A subject in their 50s · a clinical photograph showing a skin lesion.
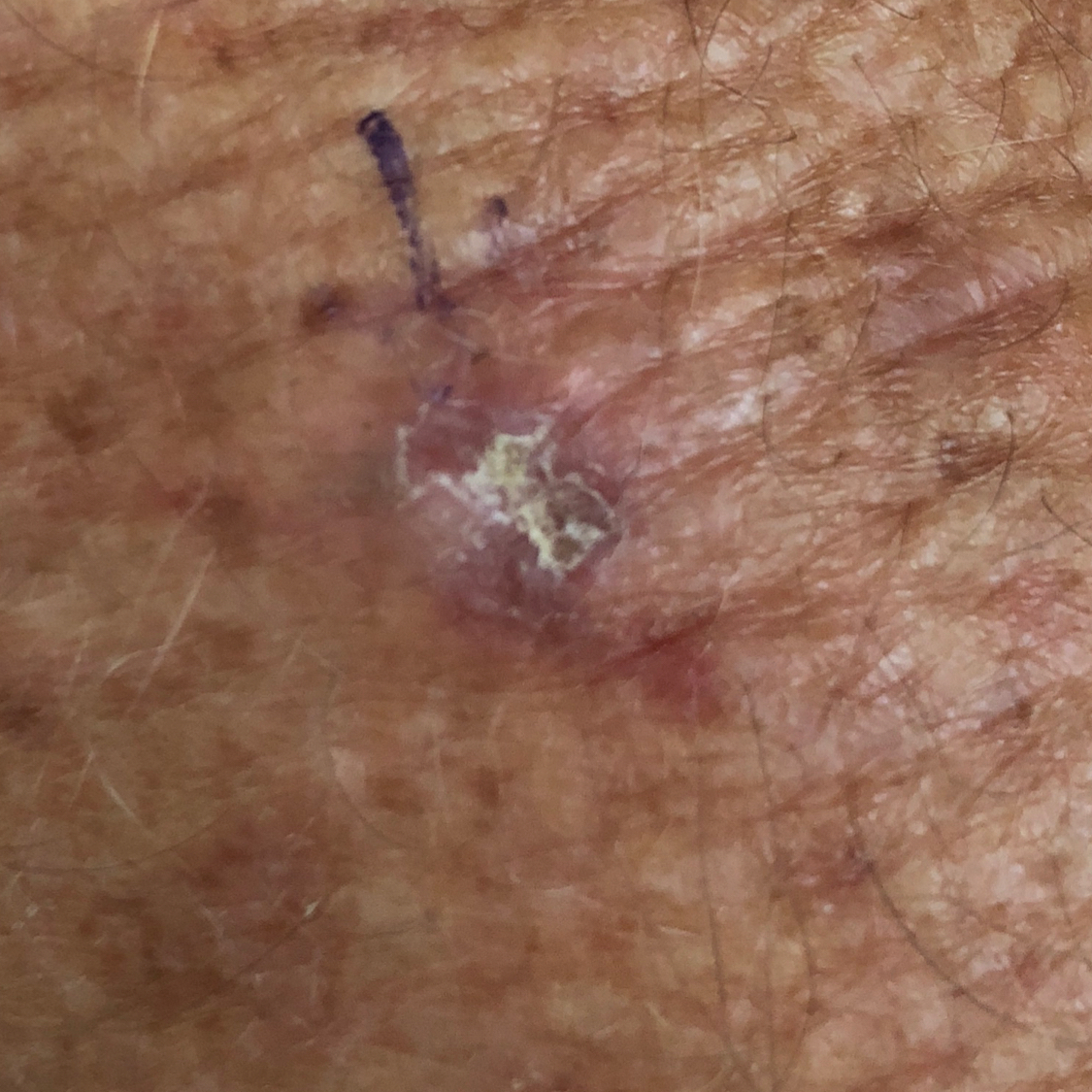patient-reported symptoms: growth, itching / no elevation; assessment: actinic keratosis (clinical consensus).